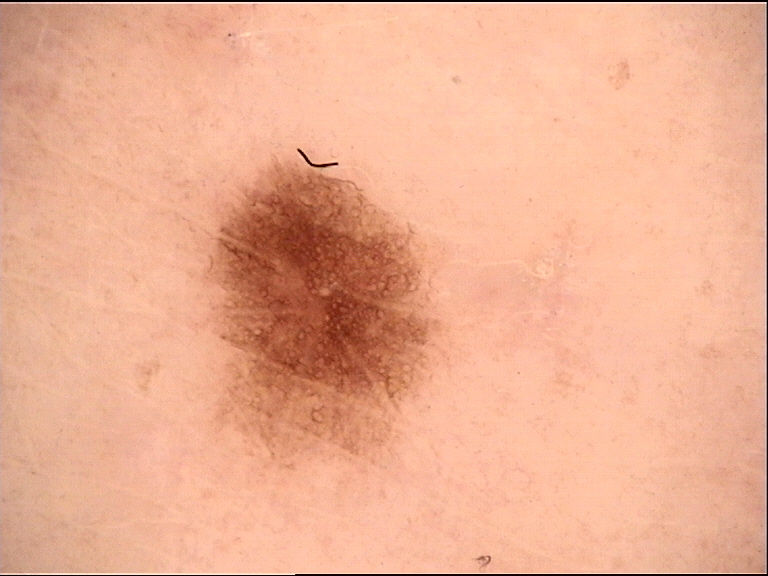image — dermatoscopy
label — dysplastic junctional nevus (expert consensus)